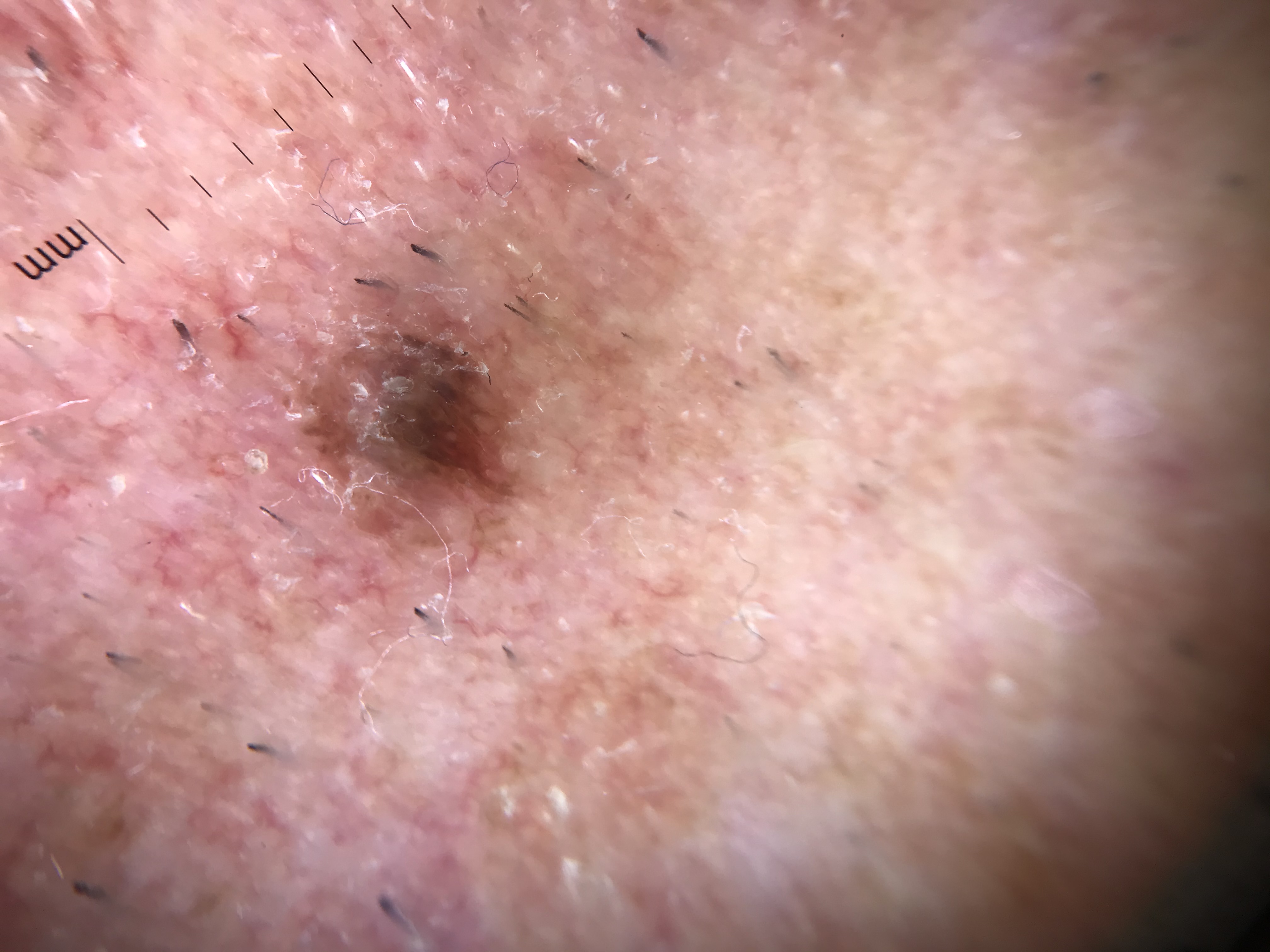Findings:
A dermoscopic photograph of a skin lesion. The architecture is that of a keratinocytic lesion.
Conclusion:
The diagnosis was a benign lesion — a seborrheic keratosis.